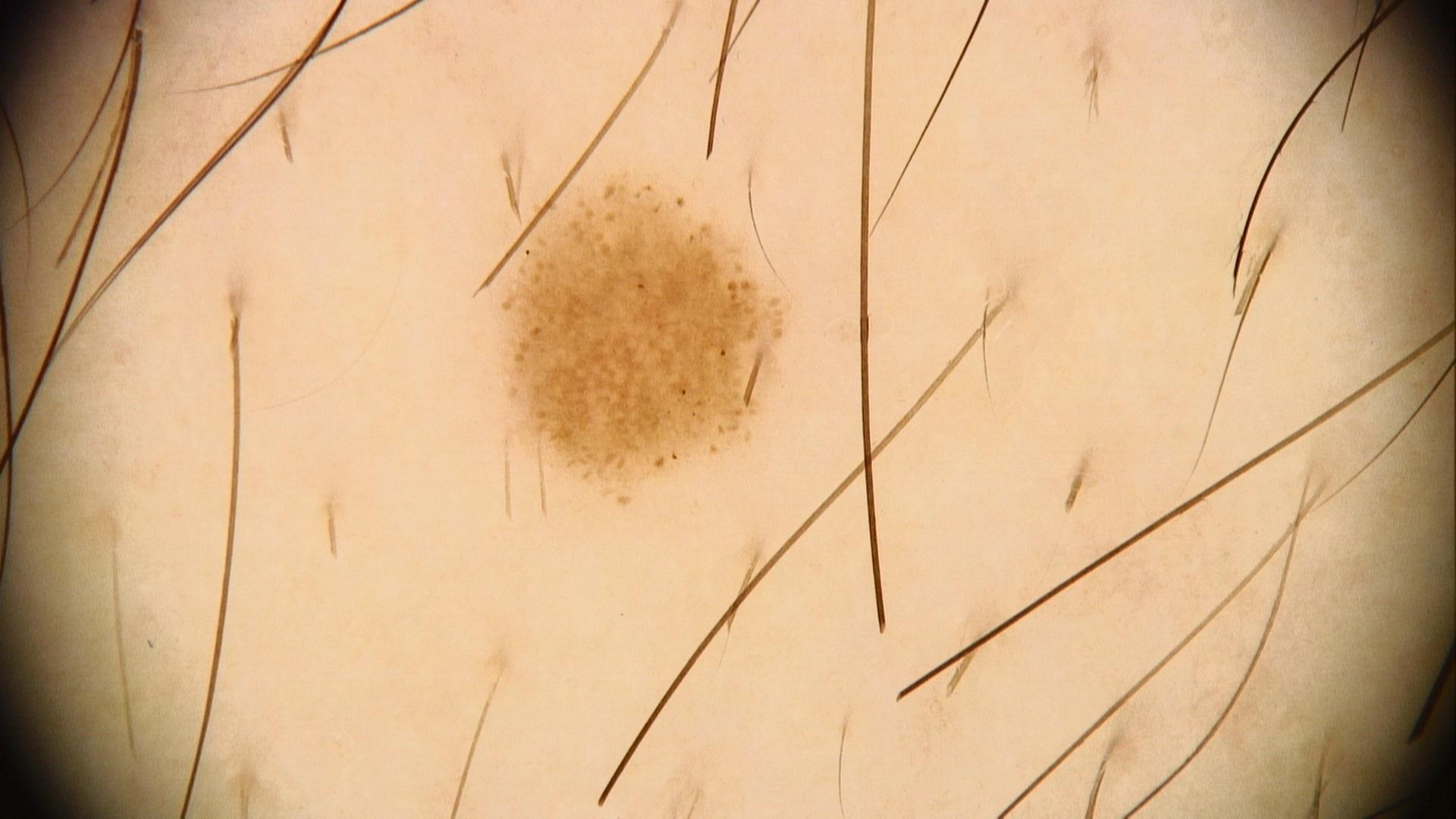Case:
- melanoma history · no prior melanoma and no melanoma in first-degree relatives
- subject · male, about 20 years old
- image type · contact-polarized dermoscopy
- anatomic site · an upper extremity
- assessment · Nevus